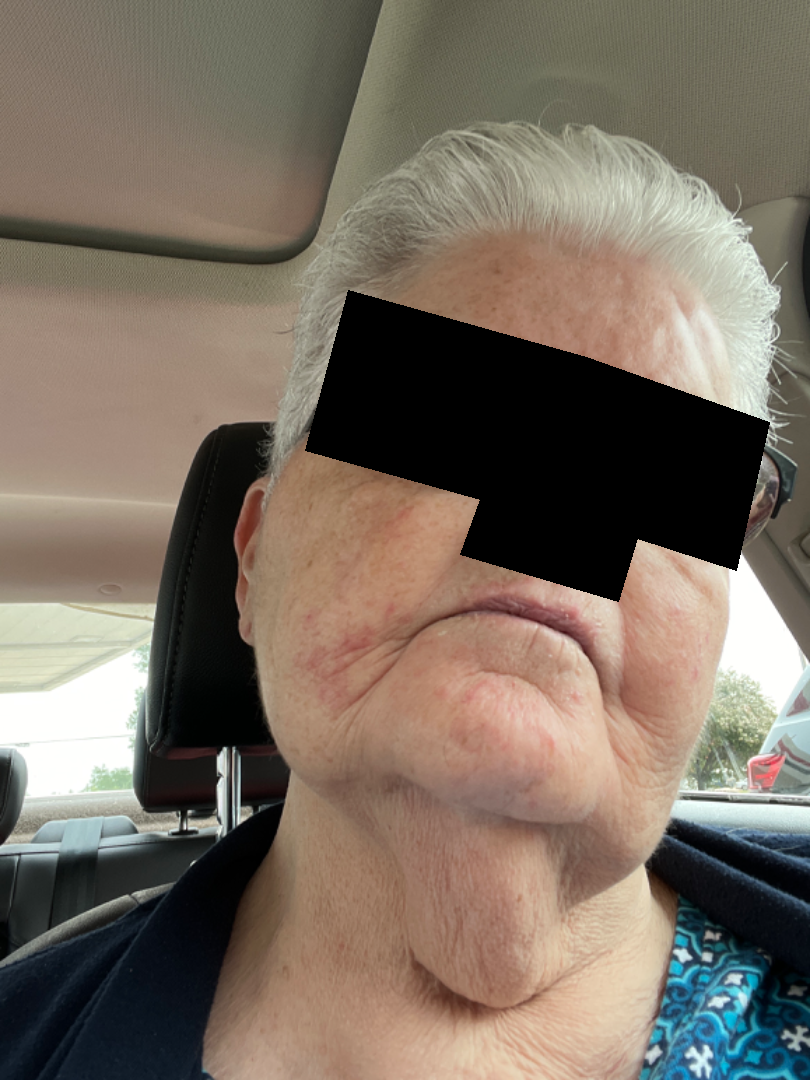assessment: could not be assessed